A dermoscopic photograph of a skin lesion:
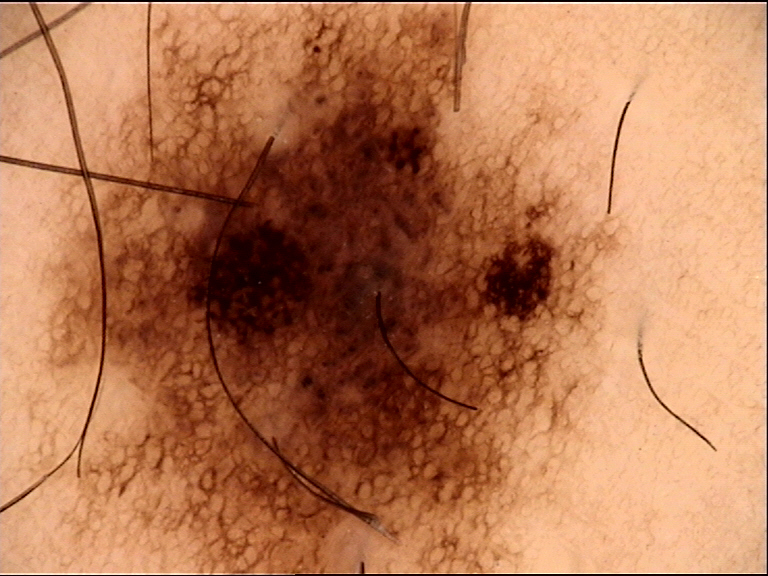Findings:
• diagnostic label · dysplastic compound nevus (expert consensus)